Close-up view, the patient is male — 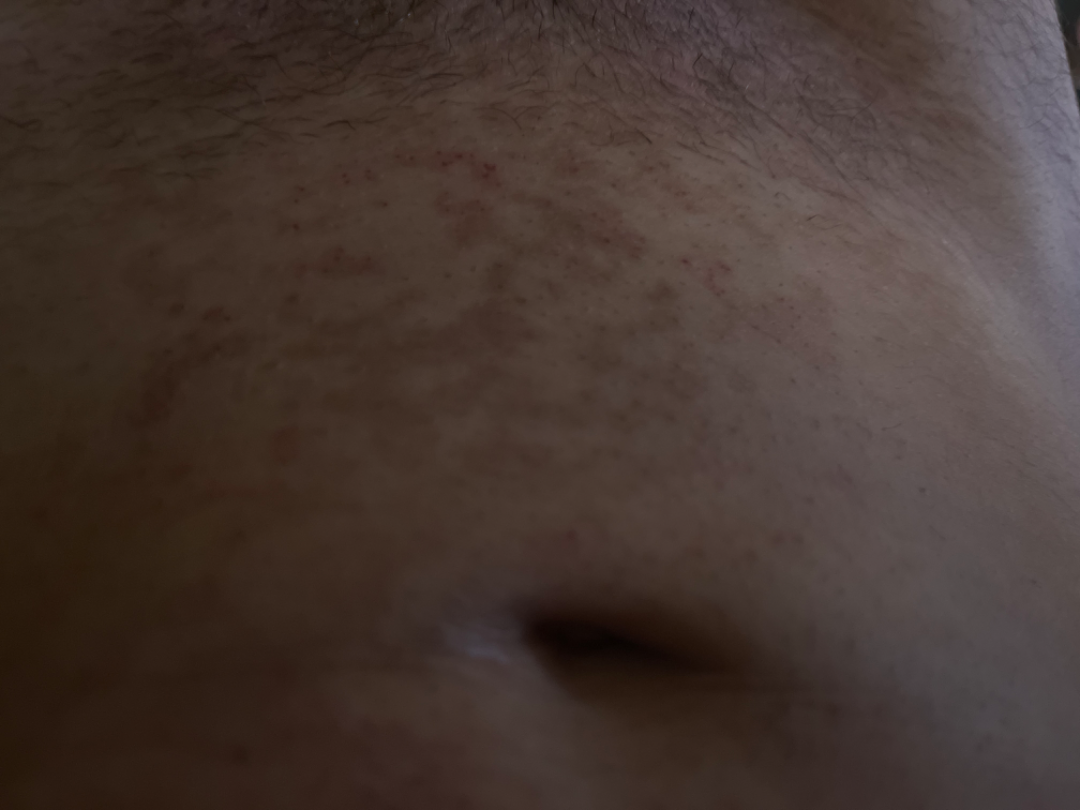Most likely Confluent and reticulate papillomatosis; with consideration of Tinea Versicolor; also consider Post-Inflammatory hyperpigmentation.